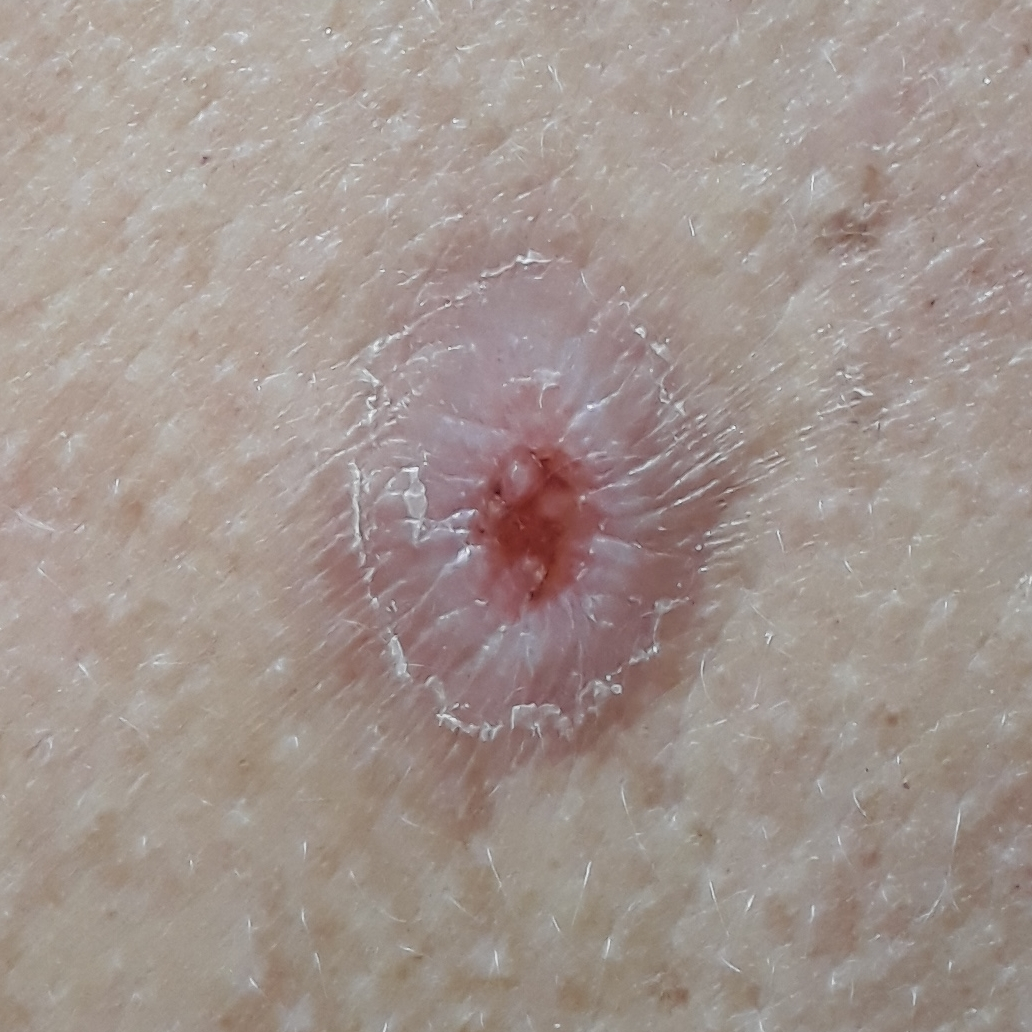A clinical photograph showing a skin lesion. A female patient in their late 50s. The chart notes prior skin cancer (patient or family) and prior malignancy (patient or family). Measuring about 13 × 12 mm. Per patient report, the lesion has changed, itches, has grown, has bled, and hurts, but is not elevated. Histopathologically confirmed as a squamous cell carcinoma.